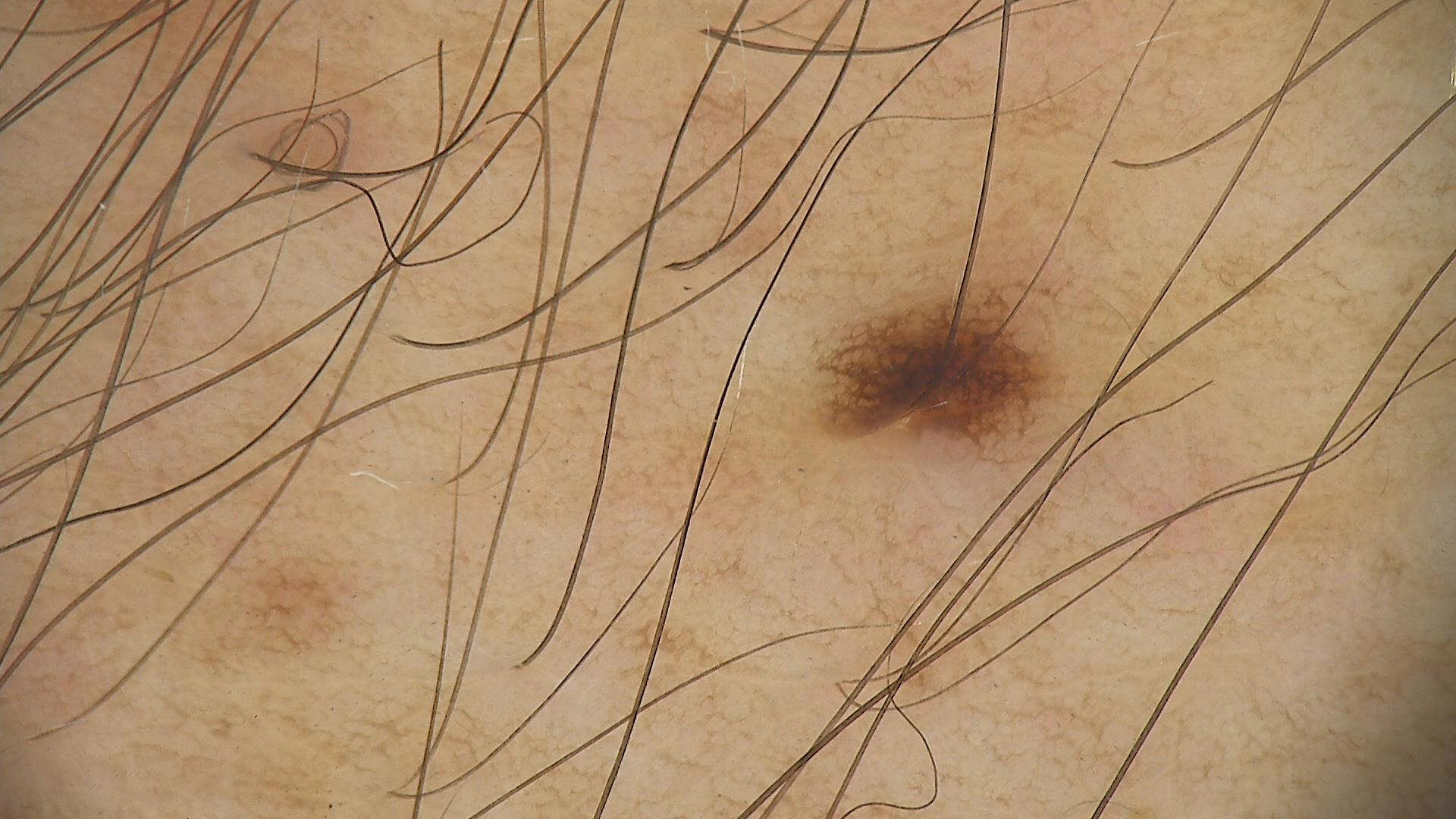A dermatoscopic image of a skin lesion. Consistent with a dysplastic junctional nevus.